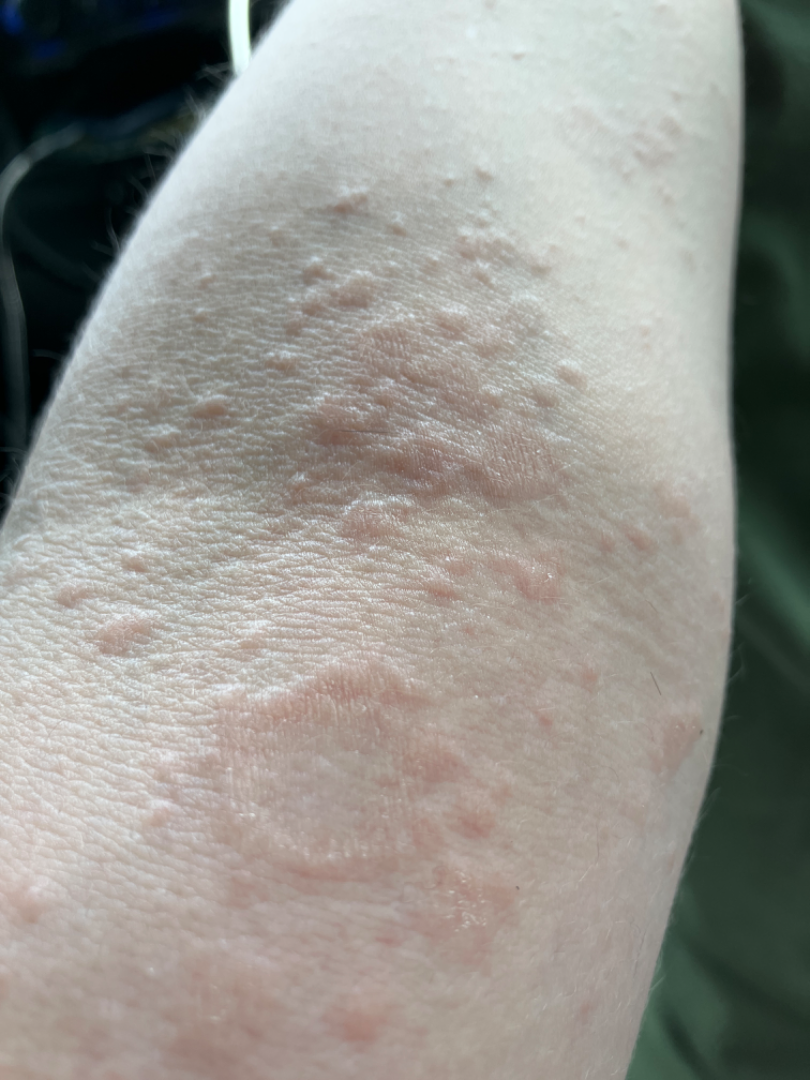Background:
The lesion is associated with enlargement and bothersome appearance. The contributor is a female aged 30–39. The patient reported no systemic symptoms. Close-up view. Self-categorized by the patient as a rash. The patient reports the lesion is raised or bumpy. Present for one to four weeks. The lesion involves the leg, arm and front of the torso.
Findings:
On remote review of the image: Urticaria (0.67); Tinea Versicolor (0.11); Allergic Contact Dermatitis (0.11); Eczema (0.11).